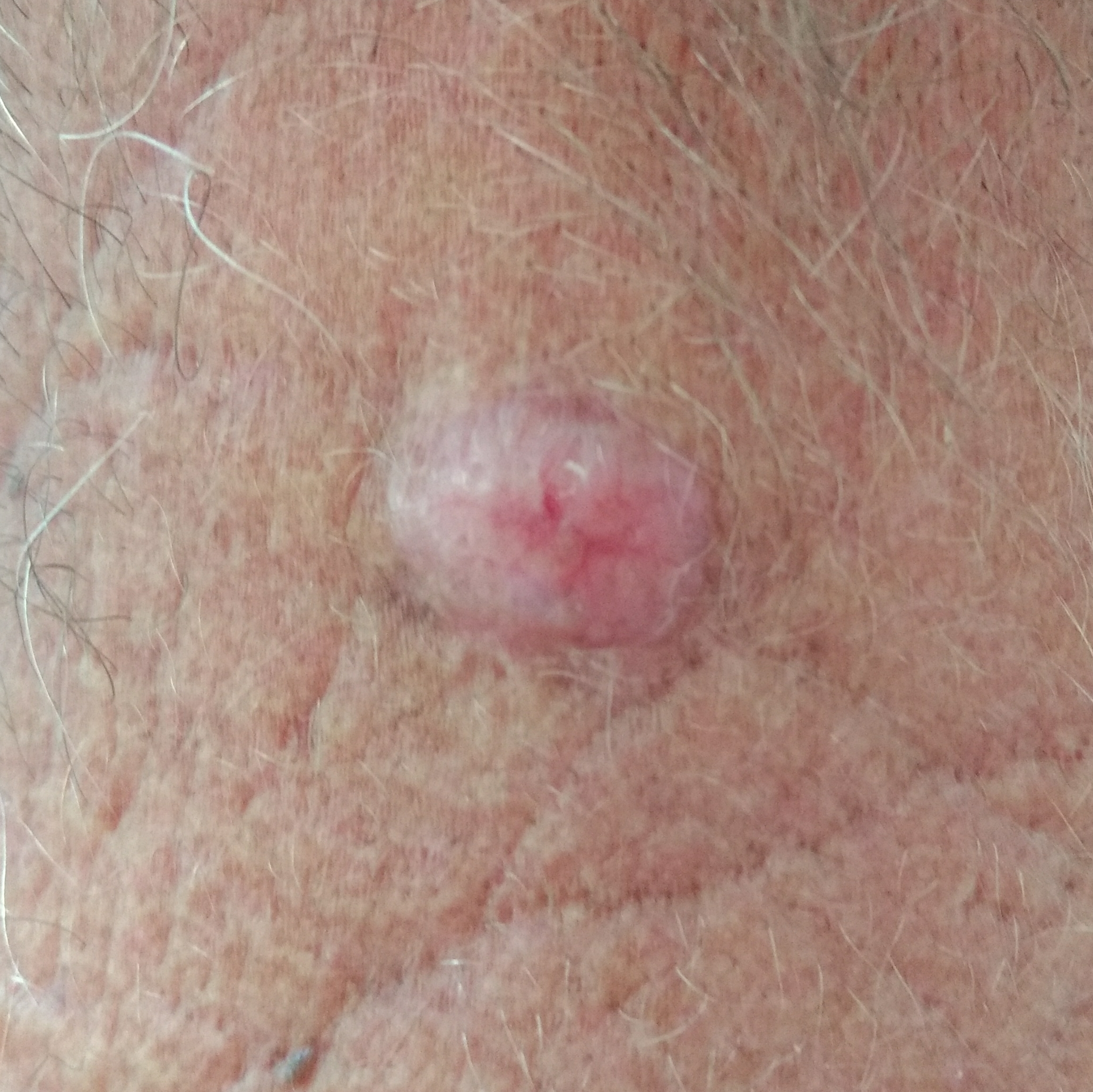Q: What are the relevant risk factors?
A: tobacco use, alcohol use, pesticide exposure
Q: How was this image acquired?
A: clinical photo
Q: Tell me about the patient.
A: male, in their 60s
Q: Skin phototype?
A: II
Q: What is the anatomic site?
A: the neck
Q: How large is the lesion?
A: 14x8 mm
Q: Any reported symptoms?
A: bleeding, growth, elevation
Q: What is the diagnosis?
A: basal cell carcinoma (biopsy-proven)